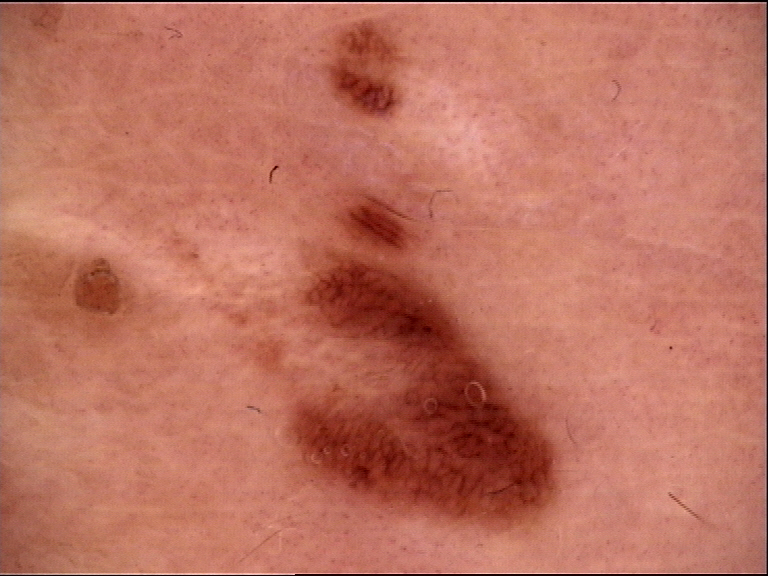category=dysplastic
label=recurrent nevus (expert consensus)